Dermoscopy of a skin lesion:
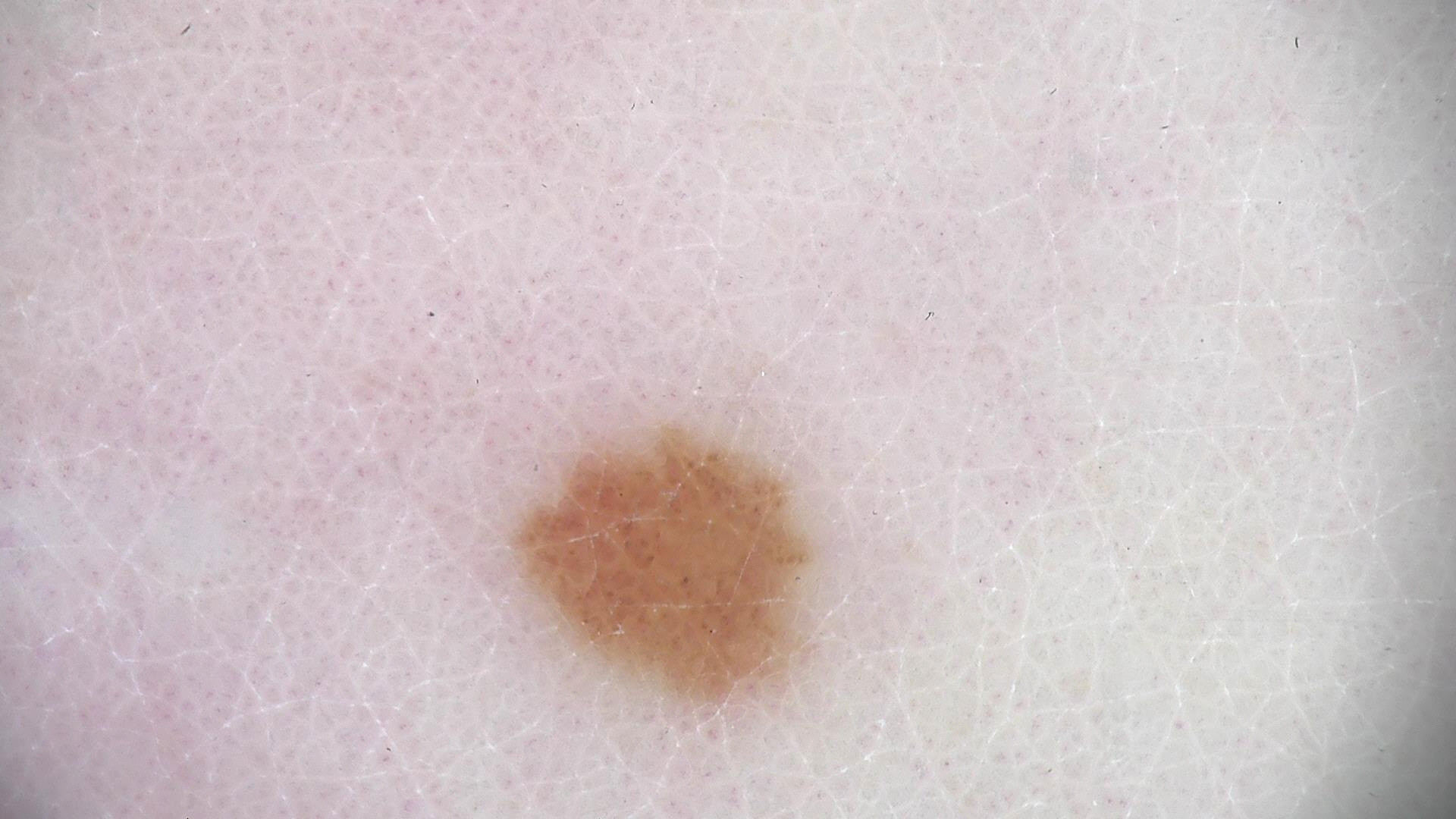Q: What was the diagnostic impression?
A: acral dysplastic junctional nevus (expert consensus)